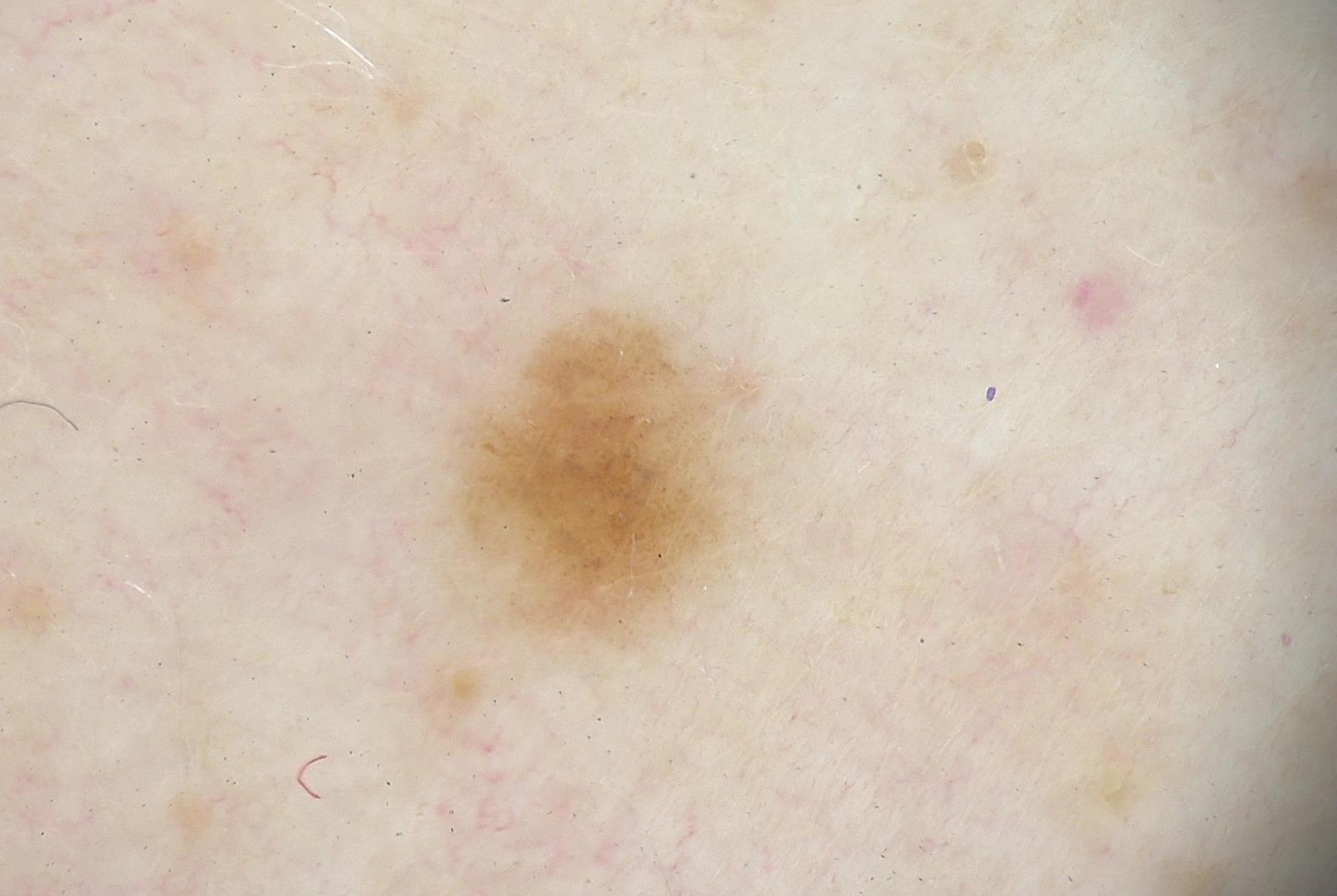Consistent with a benign lesion — a dysplastic junctional nevus.